A dermoscopy image of a single skin lesion.
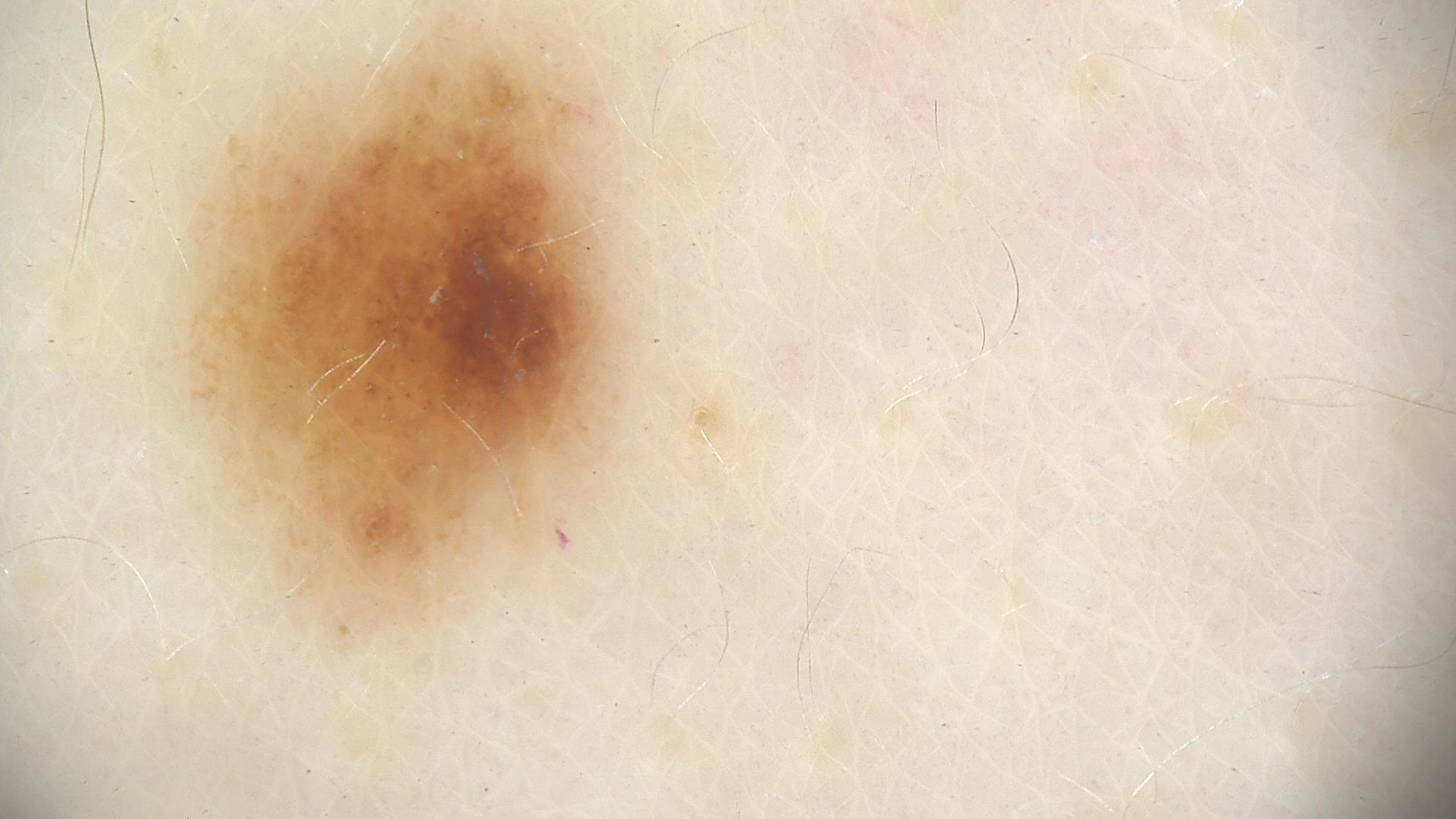The diagnosis was a benign lesion — a dysplastic junctional nevus.